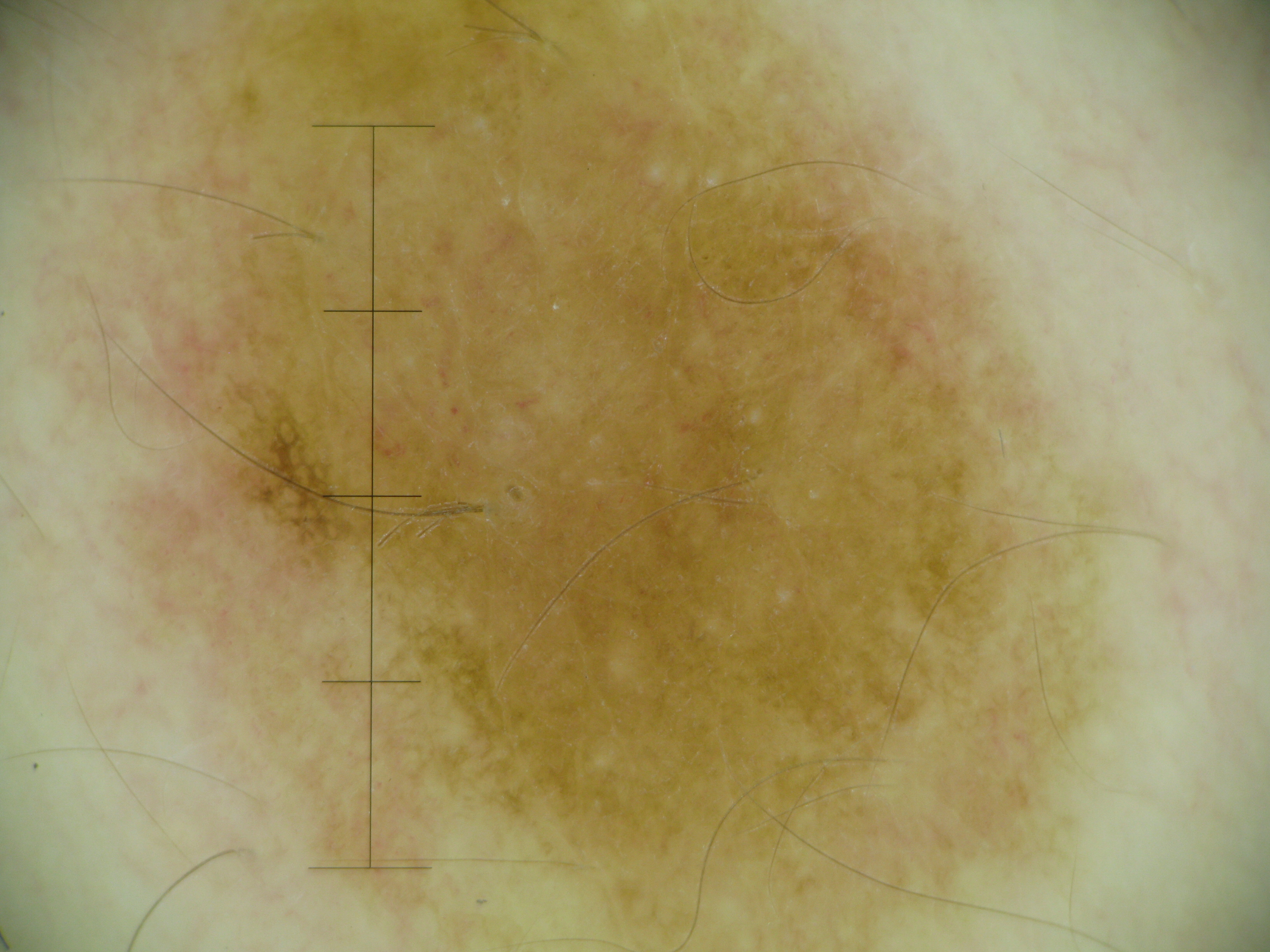imaging: dermoscopy; label: dysplastic compound nevus (expert consensus).